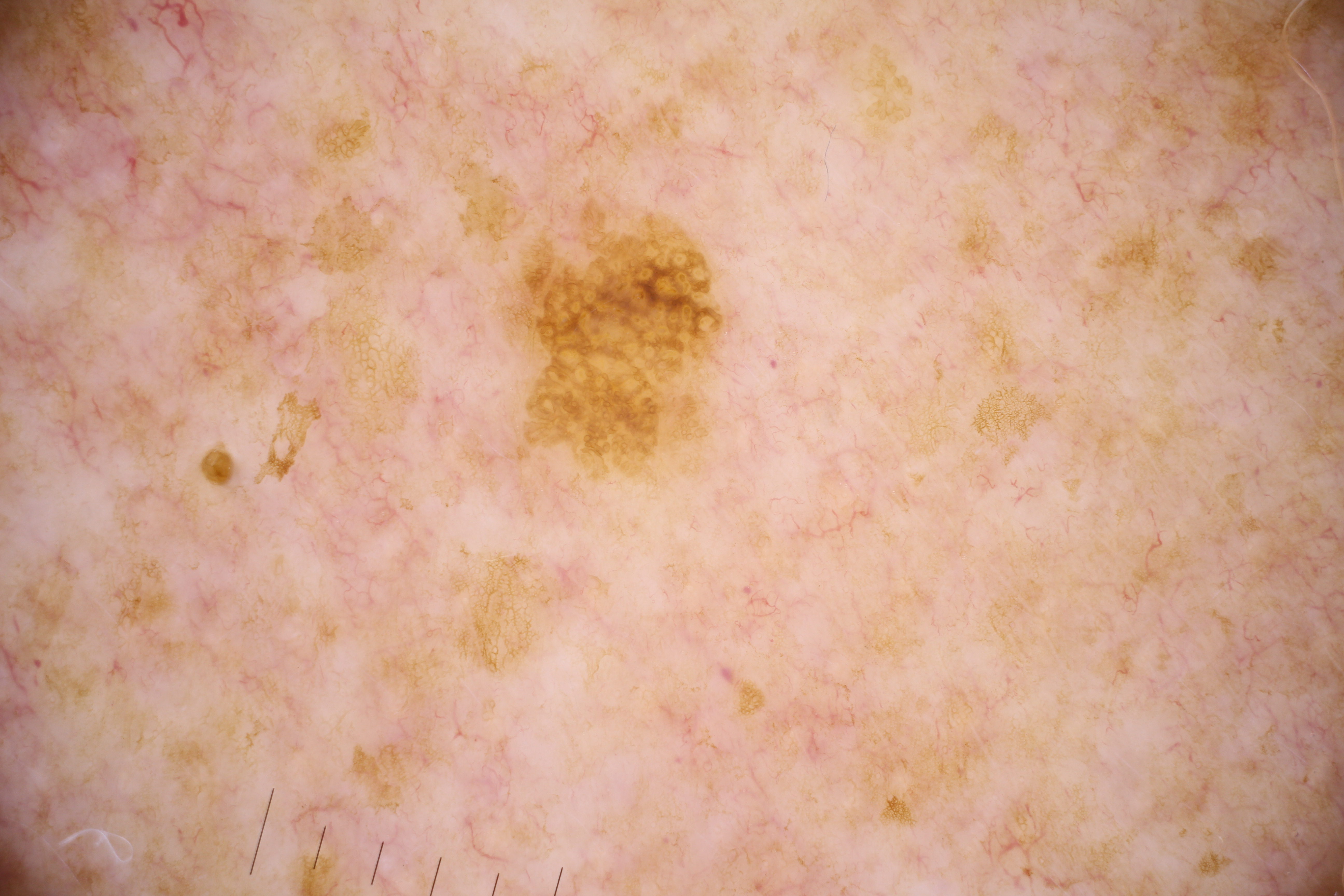A dermatoscopic image of a skin lesion.
Lesion location: x1=515 y1=224 x2=725 y2=462.
Expert review diagnosed this as a seborrheic keratosis.